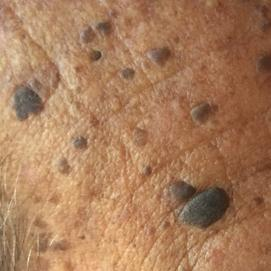| key | value |
|---|---|
| skin type | IV |
| image | clinical photograph |
| risk factors | alcohol use, no pesticide exposure |
| location | the face |
| lesion diameter | 8 × 6 mm |
| patient-reported symptoms | growth, elevation |
| diagnostic label | seborrheic keratosis (clinical consensus) |